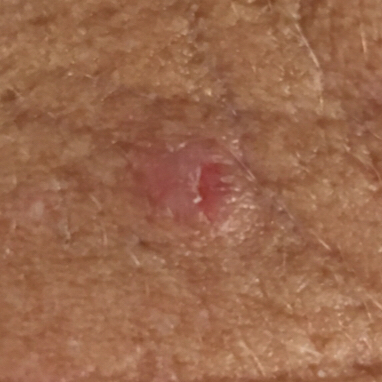skin_type: III
risk_factors:
  positive:
    - prior cancer (patient or family)
  negative:
    - smoking
    - pesticide exposure
patient:
  age: 57
  gender: female
image: clinical photograph
lesion_location: the neck
lesion_size:
  diameter_1_mm: 7.0
  diameter_2_mm: 5.0
symptoms:
  present:
    - itching
    - bleeding
    - elevation
  absent:
    - pain
    - growth
diagnosis:
  name: actinic keratosis
  code: ACK
  malignancy: indeterminate
  confirmation: histopathology